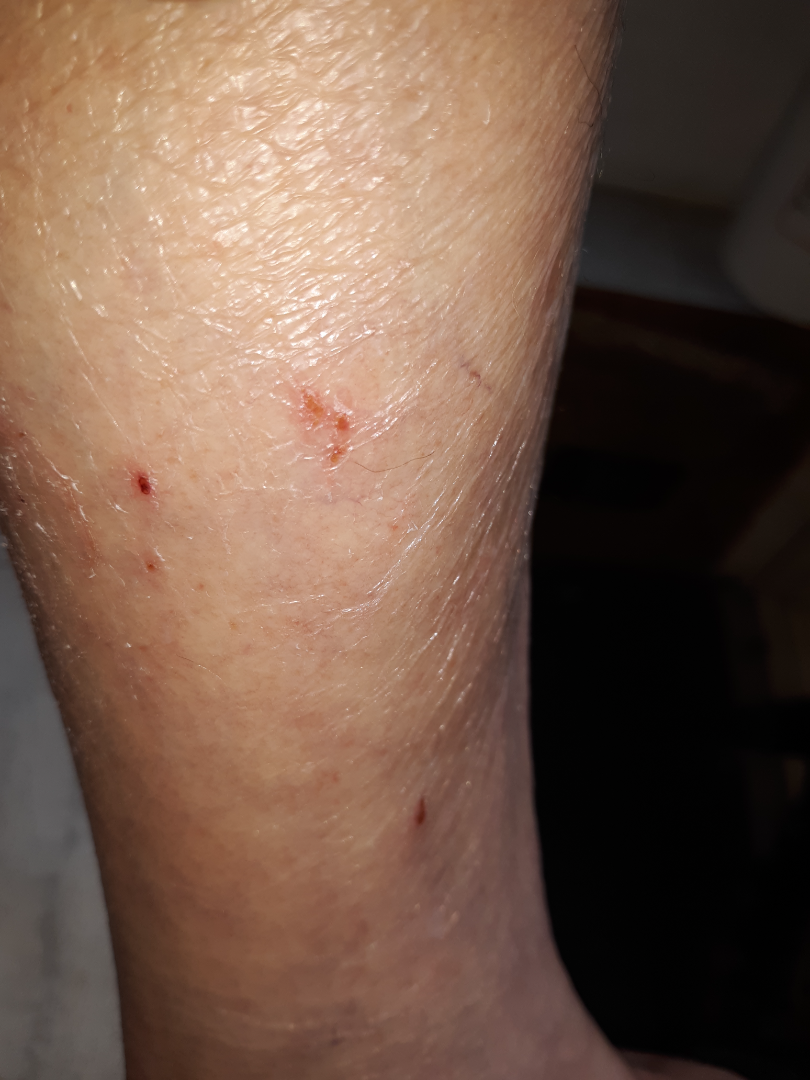The patient indicates associated shortness of breath, fatigue and joint pain. The patient indicates itching, enlargement and bleeding. The leg is involved. The patient indicates the condition has been present for one to three months. The patient considered this a rash. The patient indicates the lesion is rough or flaky and raised or bumpy. This image was taken at an angle. Xerosis (considered); Eczema (considered); Ichthyosis (remote).